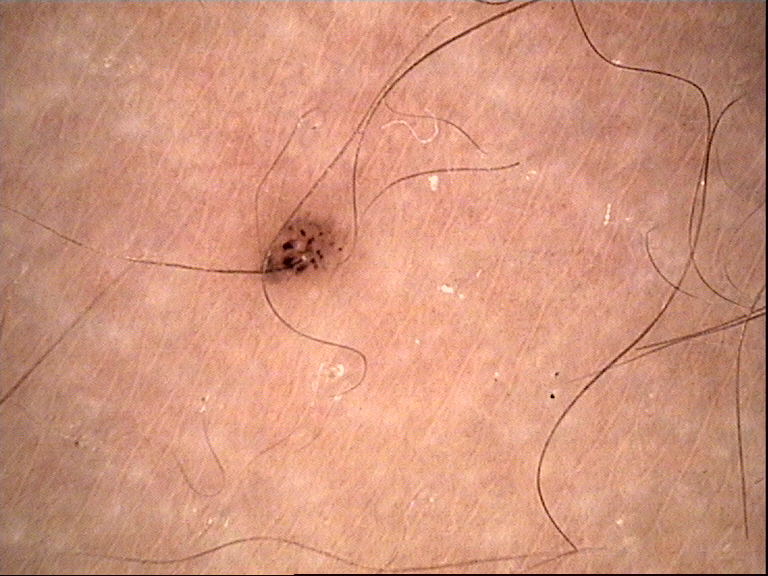Dermoscopy of a skin lesion.
Diagnosed as a benign lesion — a dysplastic junctional nevus.